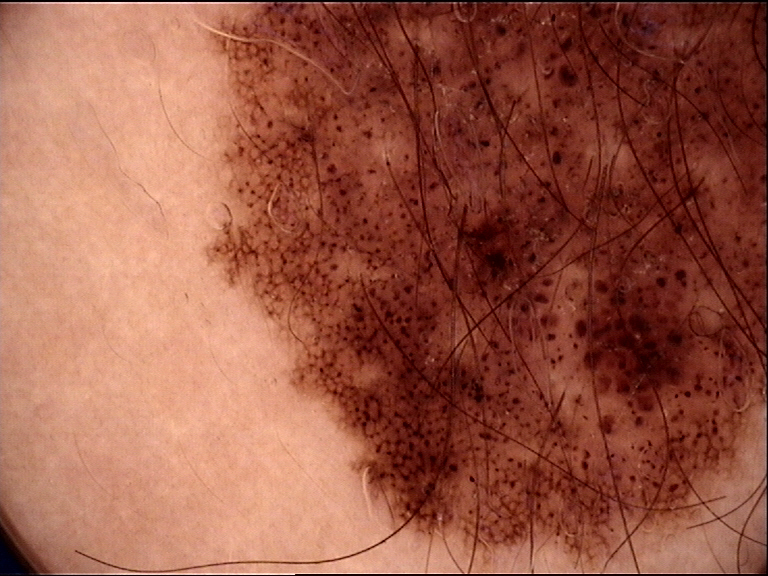The architecture is that of a banal lesion. Consistent with a congenital compound nevus.